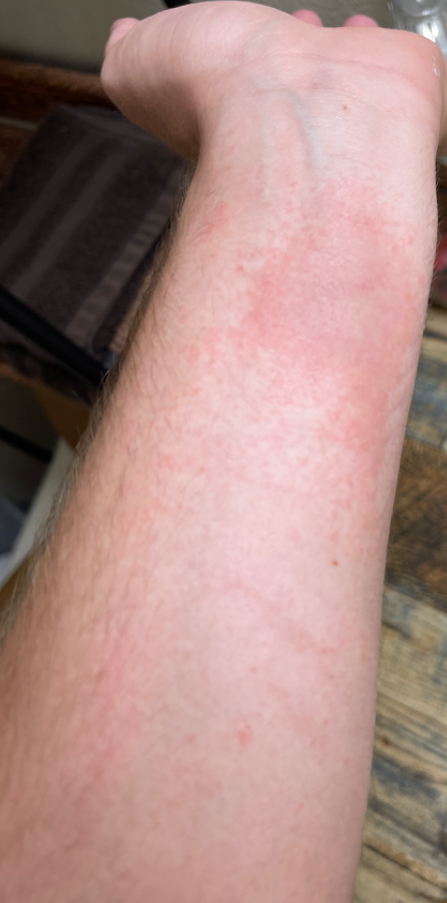  patient: male, age 18–29
  body_site: arm
  skin_tone:
    fitzpatrick: II
    monk_skin_tone: 2
  shot_type: at a distance
  symptoms:
    - itching
    - bothersome appearance
  texture: raised or bumpy
  patient_category: a rash
  duration: one to four weeks
  differential:
    Allergic Contact Dermatitis: 0.54
    Tinea: 0.23
    Eczema: 0.23